The lesion involves the palm, sole of the foot, back of the hand and top or side of the foot; the subject is a male aged 18–29; close-up view.
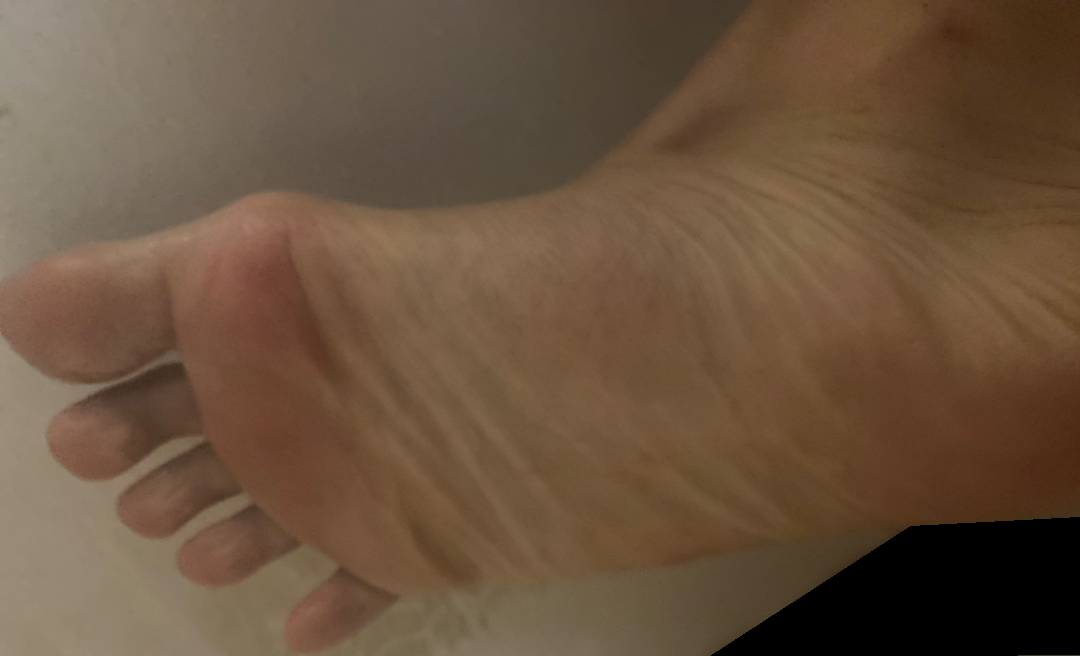| key | value |
|---|---|
| assessment | no findings on review |
| symptoms | itching, enlargement and pain |
| history | about one day |
| patient's own categorization | a rash |